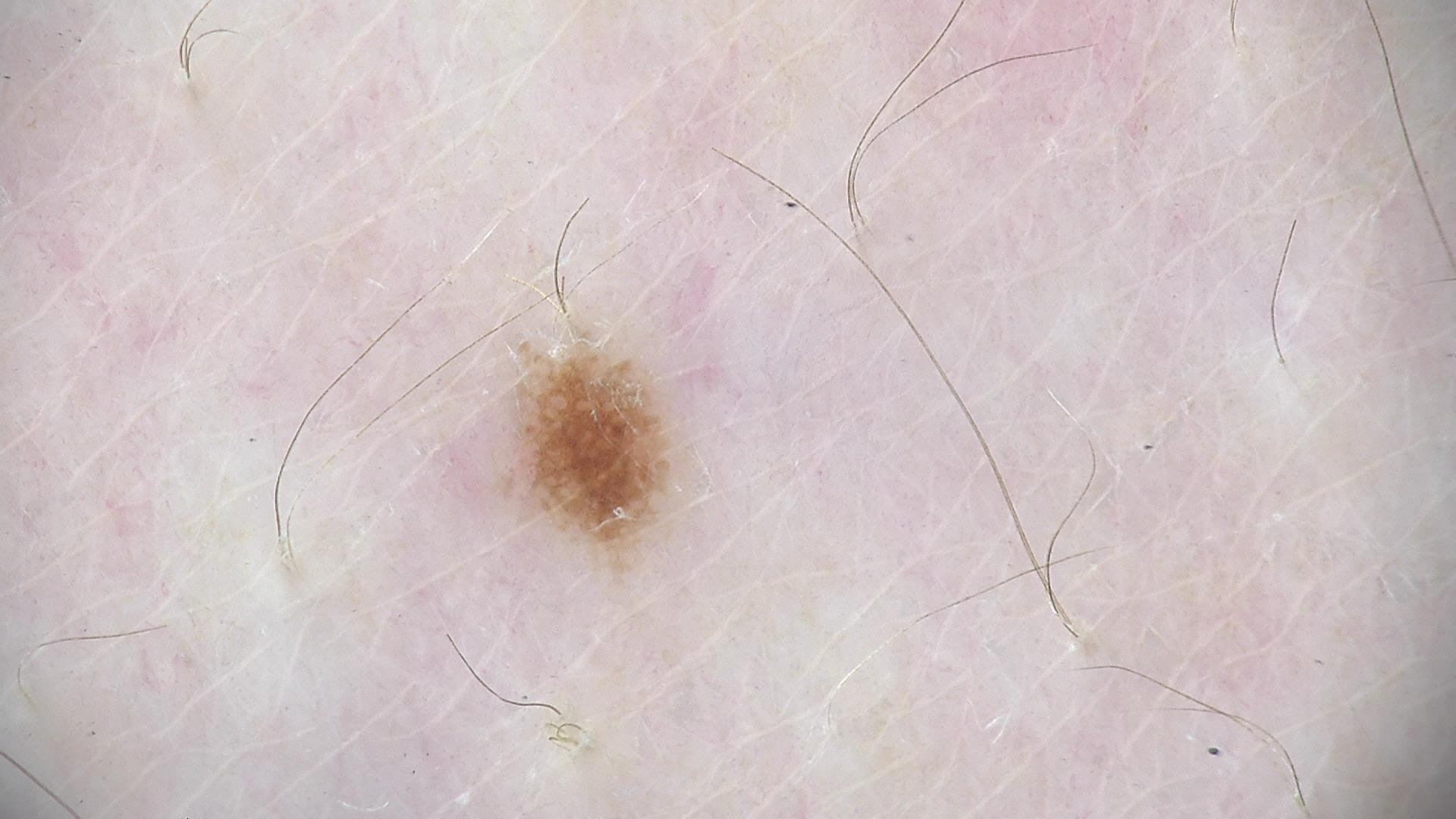{
  "image": "dermoscopy",
  "diagnosis": {
    "name": "dysplastic junctional nevus",
    "code": "jd",
    "malignancy": "benign",
    "super_class": "melanocytic",
    "confirmation": "expert consensus"
  }
}